Dermoscopy of a skin lesion, the subject is a male aged 63-67:
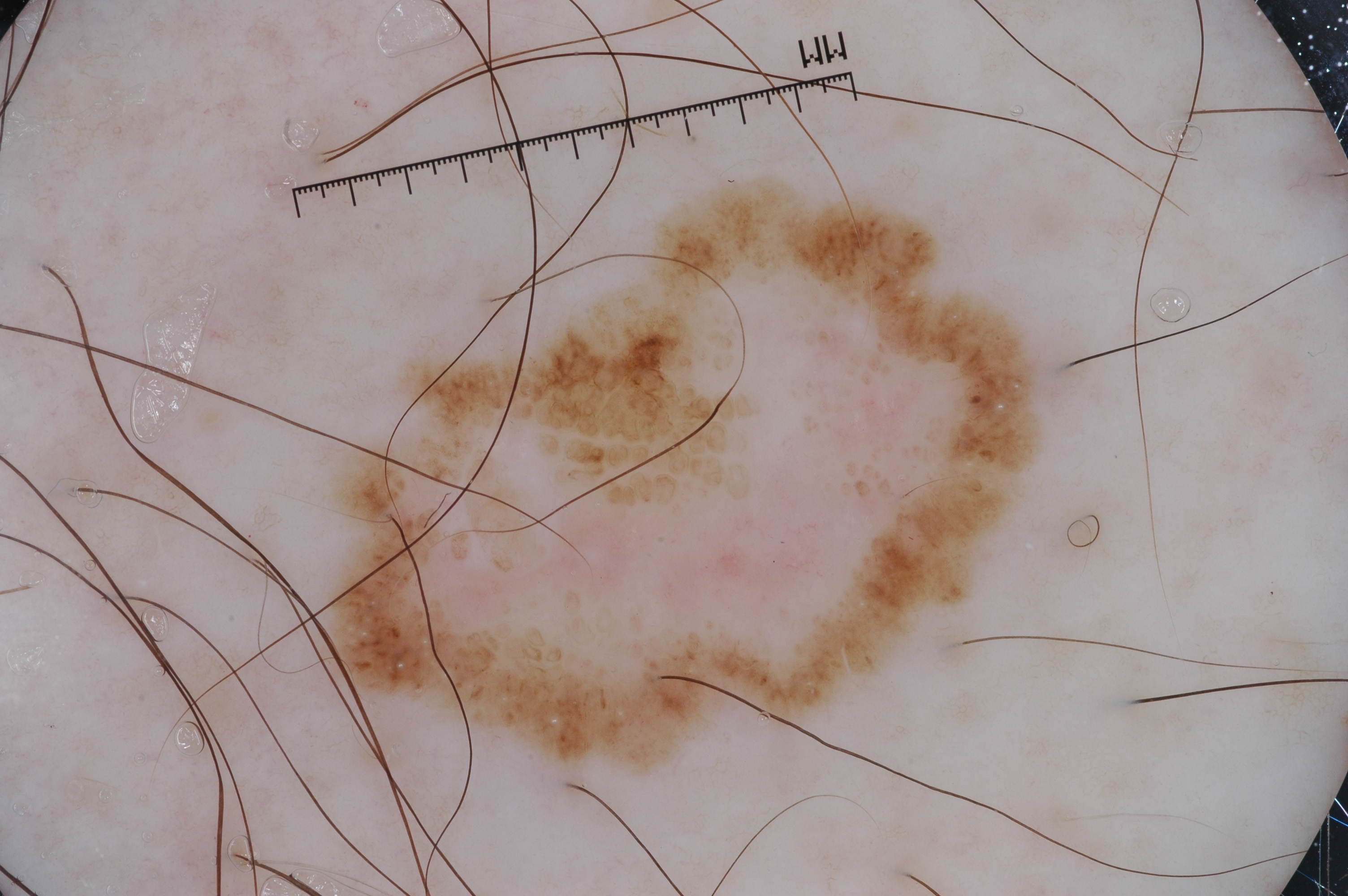  lesion_location:
    bbox_xyxy:
      - 295
      - 182
      - 1053
      - 777
  dermoscopic_features:
    present:
      - milia-like cysts
    absent:
      - negative network
      - streaks
      - pigment network
  diagnosis:
    name: seborrheic keratosis
    malignancy: benign
    lineage: keratinocytic
    provenance: clinical